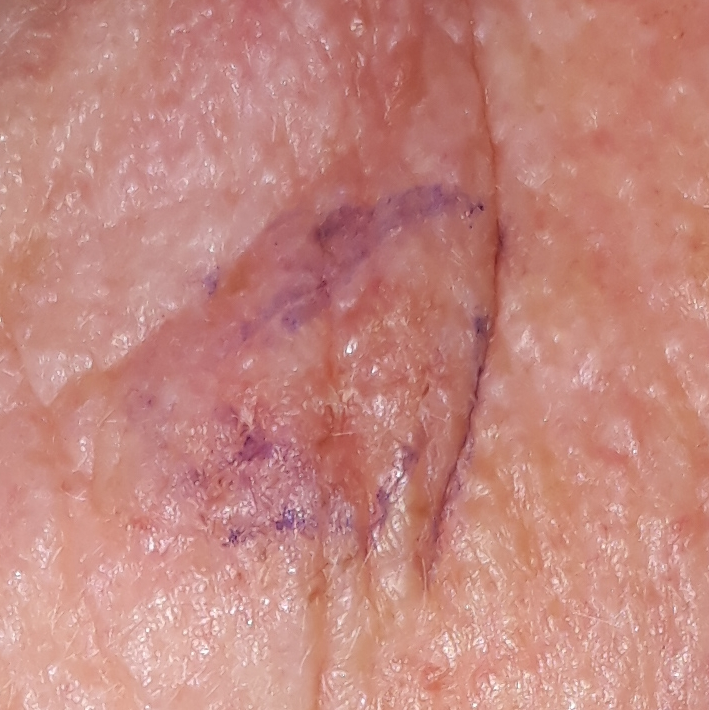| field | value |
|---|---|
| diagnostic label | actinic keratosis (clinical consensus) |